No relevant systemic symptoms · located on the leg · the condition has been present for less than one week · the patient notes the lesion is raised or bumpy · the contributor is a male aged 50–59 · no associated lesion symptoms were reported · the photograph was taken at an angle.
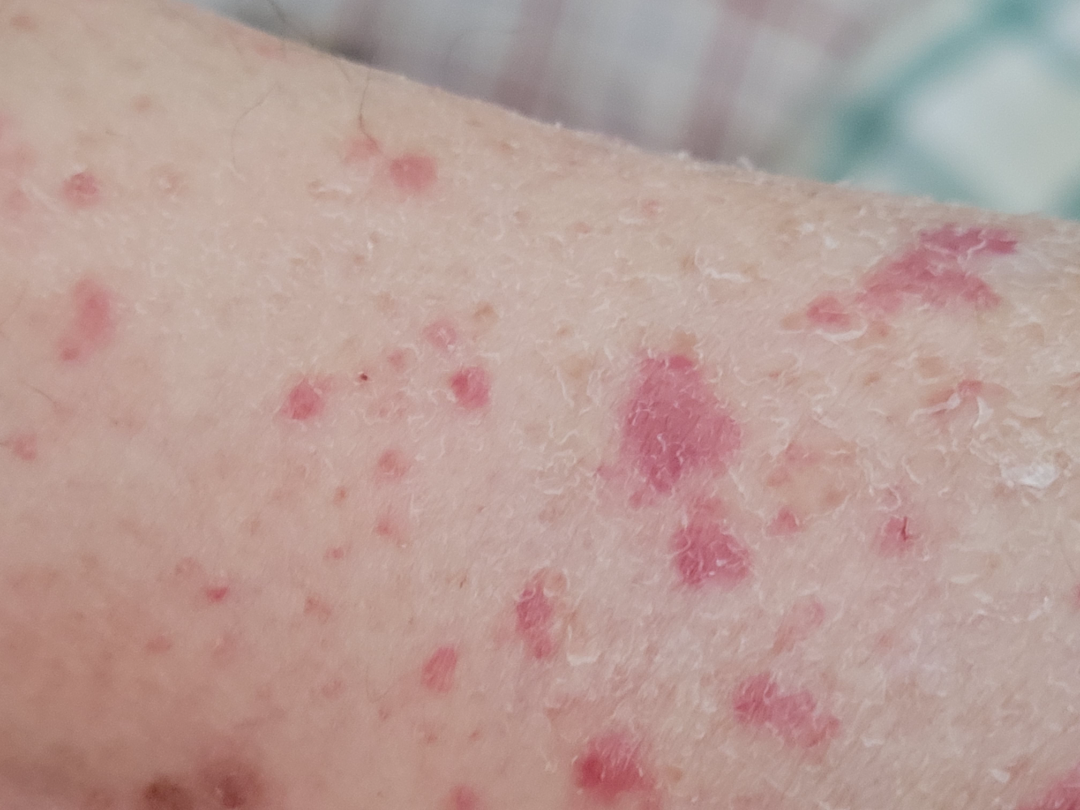assessment: not assessable.